A dermoscopy image of a single skin lesion:
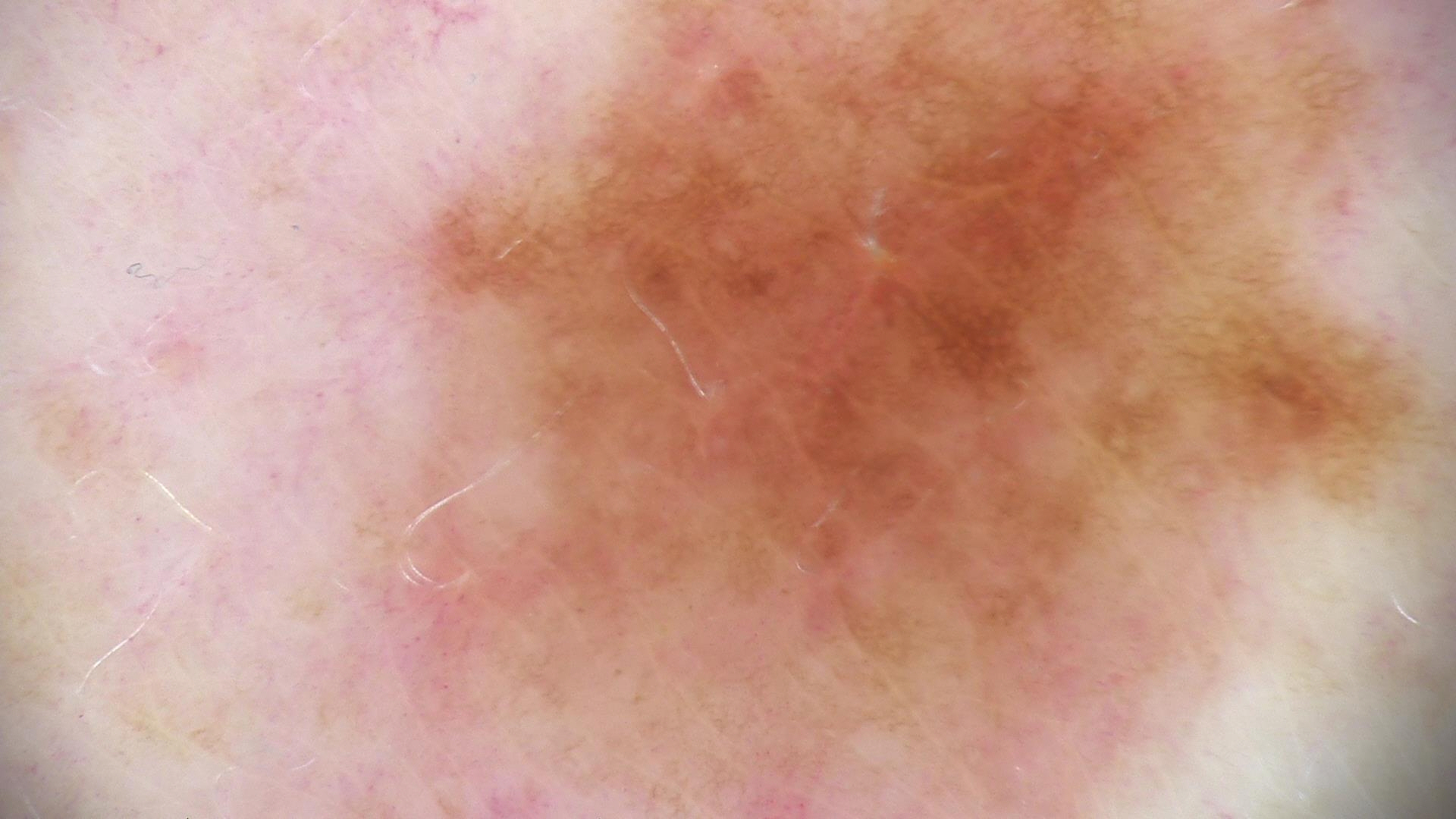label: dysplastic junctional nevus (expert consensus).